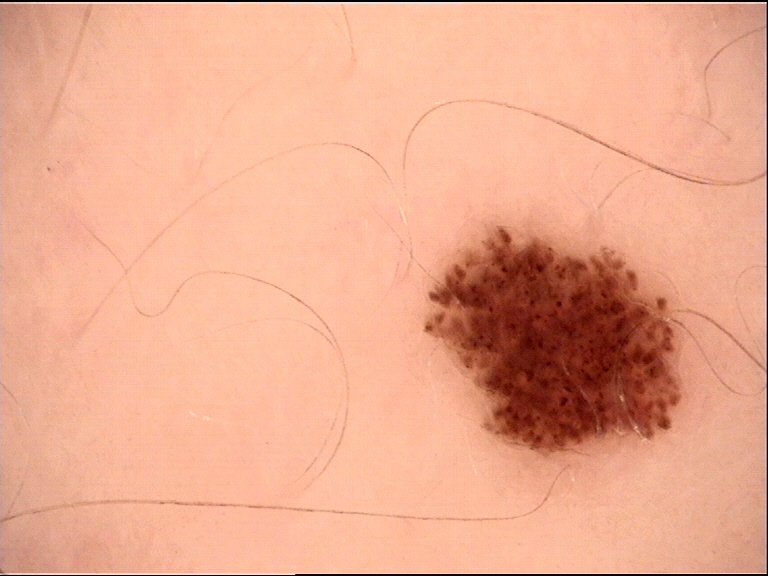Labeled as a junctional nevus.